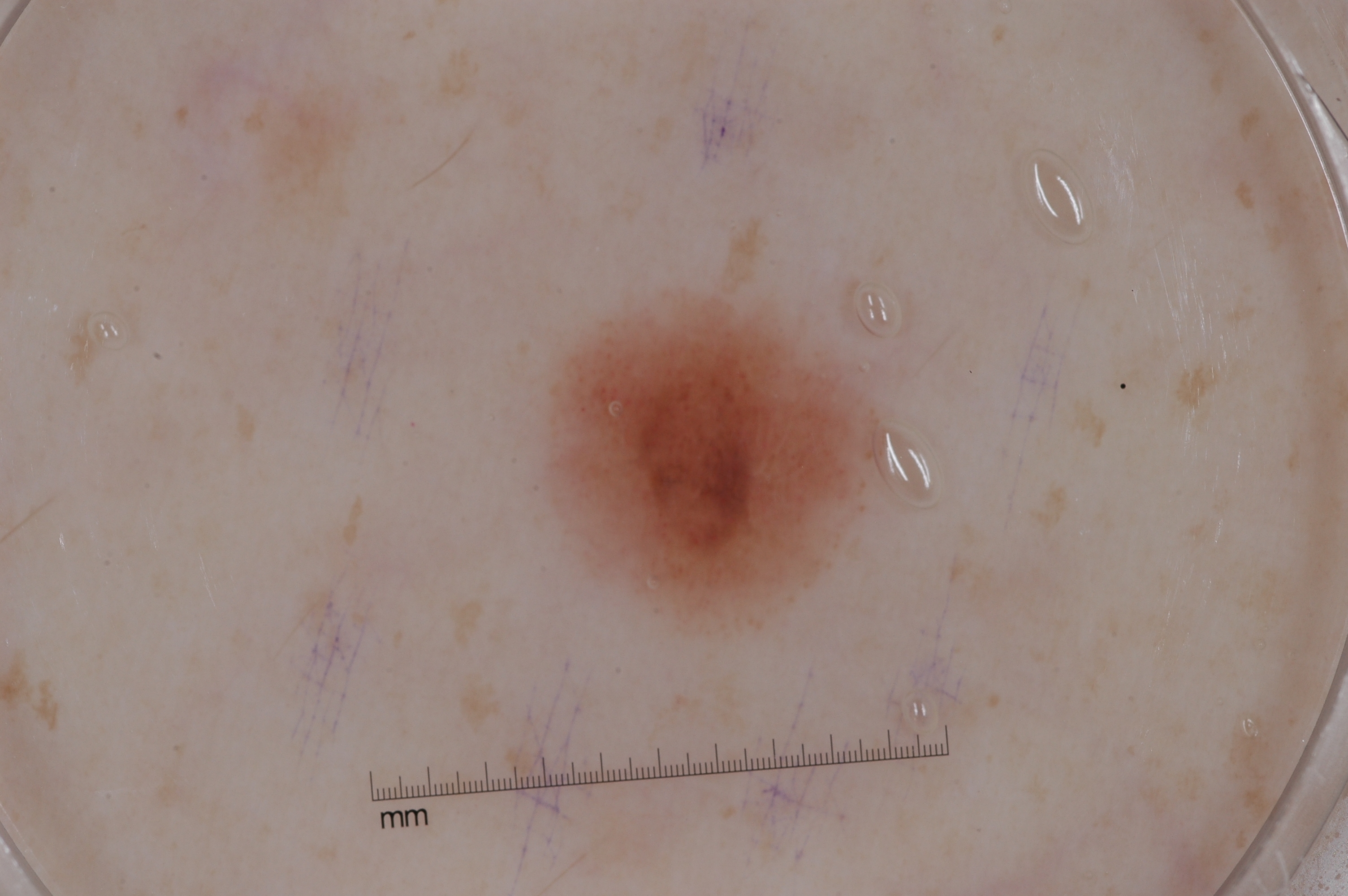imaging: dermoscopic image
dermoscopic pattern: negative network
lesion location: bbox=[548, 294, 885, 630]
lesion extent: ~7% of the field
diagnosis: a melanocytic nevus